Imaged for a research study, with no referral diagnosis recorded · a dermatoscopic image of a skin lesion · a female subject 26 years old · the patient describes having numerous moles — 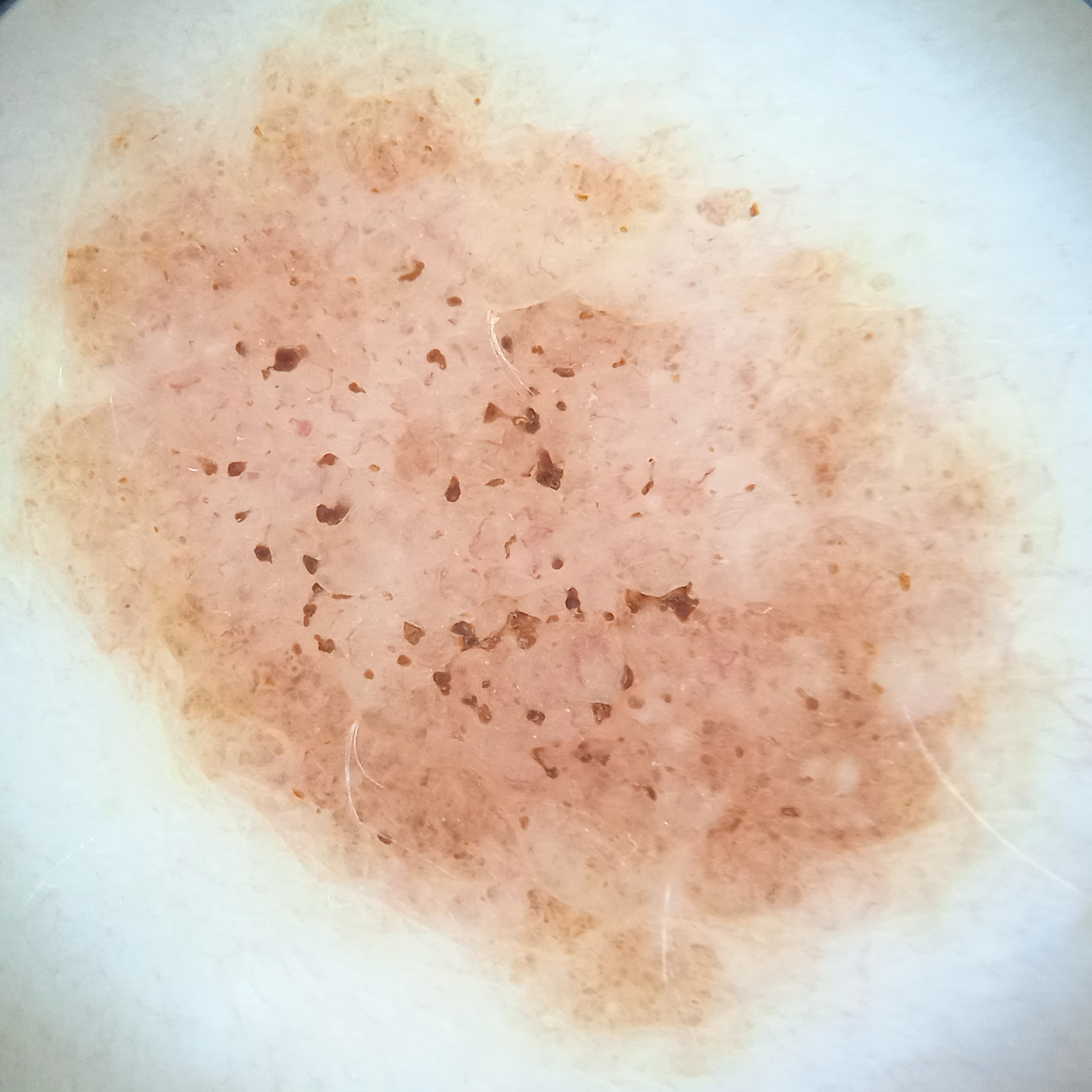Findings:
- lesion size — 13 mm
- diagnostic label — melanocytic nevus (dermatologist consensus)